A male patient, approximately 85 years of age or older; a dermoscopic close-up of a skin lesion.
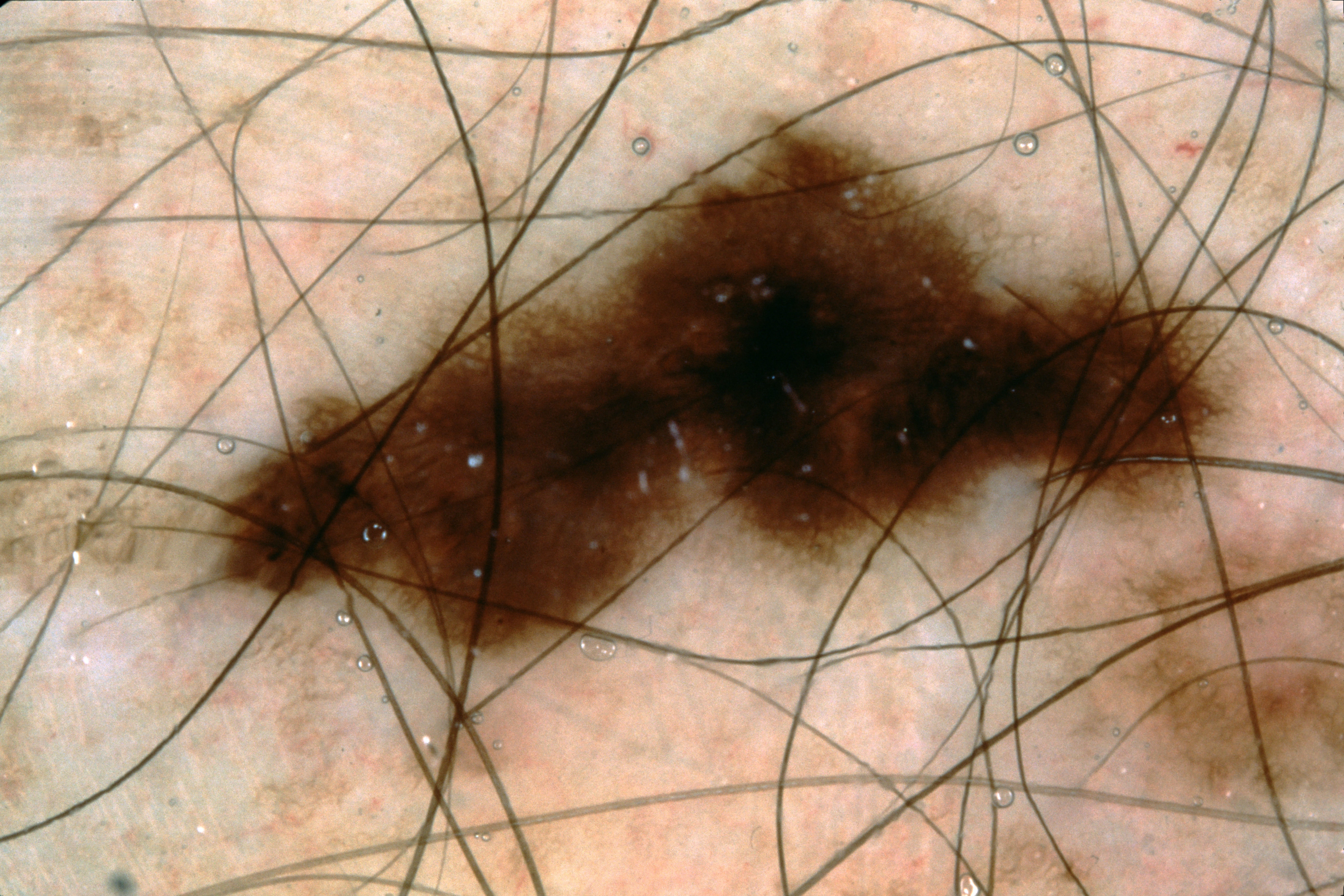extent=~35% of the field
features=pigment network
bounding box=<bbox>202, 107, 1285, 710</bbox>
impression=a melanocytic nevus